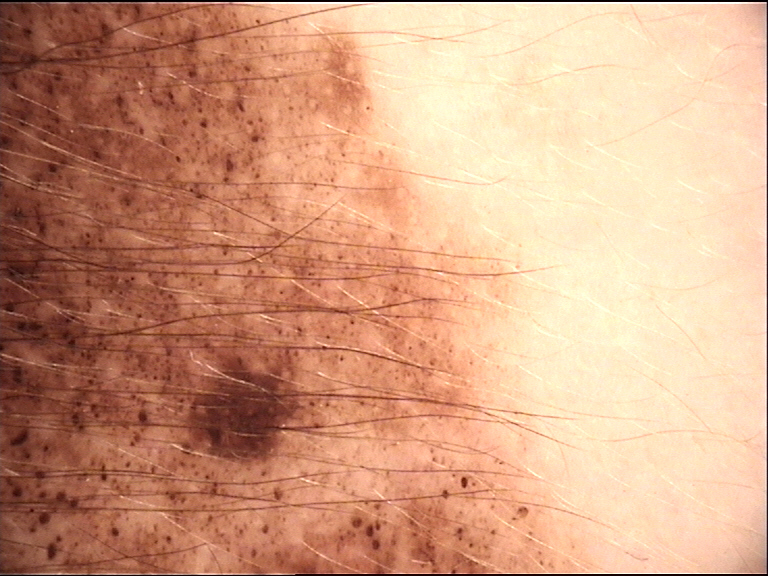diagnosis:
  name: congenital compound nevus
  code: ccb
  malignancy: benign
  super_class: melanocytic
  confirmation: expert consensus